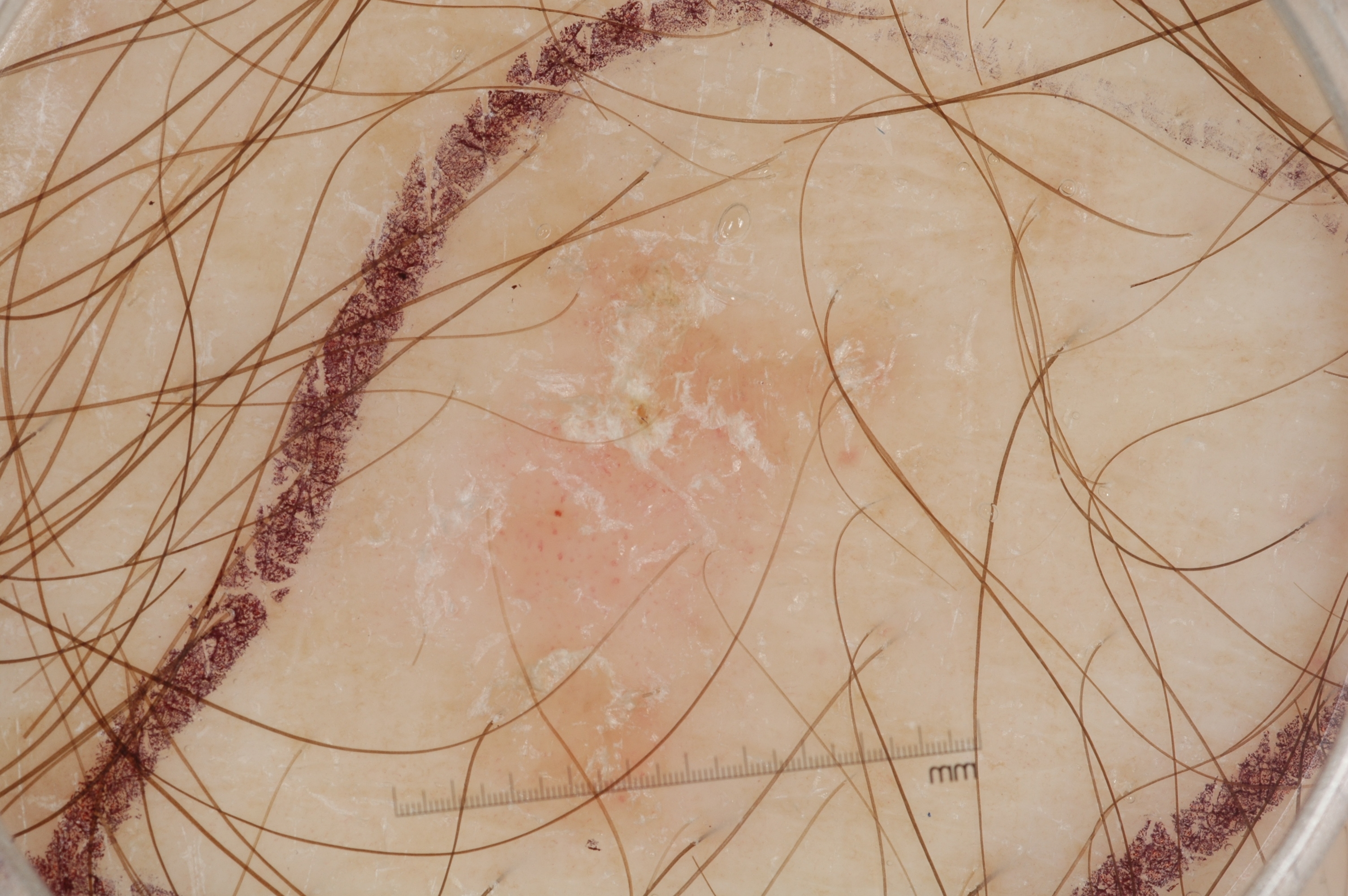Q: What kind of image is this?
A: dermoscopic image
Q: Who is the patient?
A: male, roughly 60 years of age
Q: Which dermoscopic features are absent?
A: streaks, pigment network, milia-like cysts, and negative network
Q: Lesion extent?
A: ~40% of the field
Q: Where is the lesion located?
A: 263 50 1028 893
Q: What did the assessment conclude?
A: a seborrheic keratosis, a non-melanocytic (keratinocytic) lesion